Dermoscopy of a skin lesion:
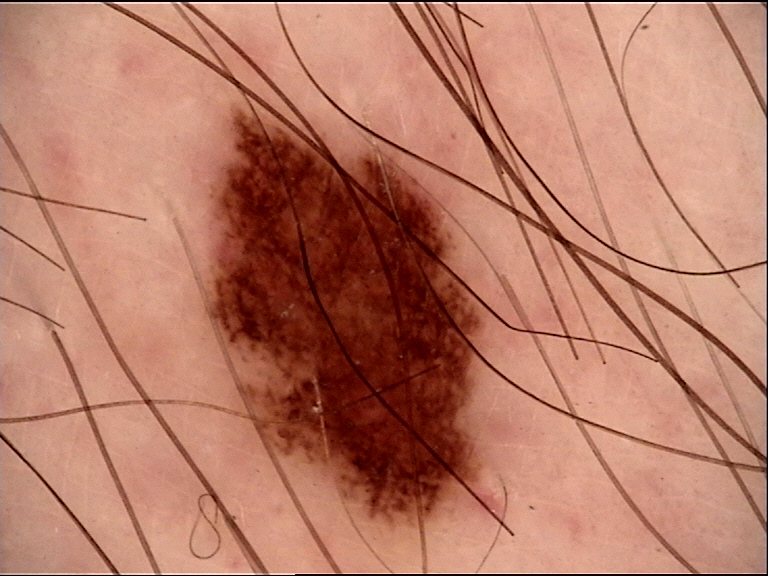<lesion>
  <diagnosis>
    <name>dysplastic junctional nevus</name>
    <code>jd</code>
    <malignancy>benign</malignancy>
    <super_class>melanocytic</super_class>
    <confirmation>expert consensus</confirmation>
  </diagnosis>
</lesion>